The photograph was taken at an angle. The contributor is a female aged 50–59. The affected area is the leg, front of the torso, arm and back of the torso — 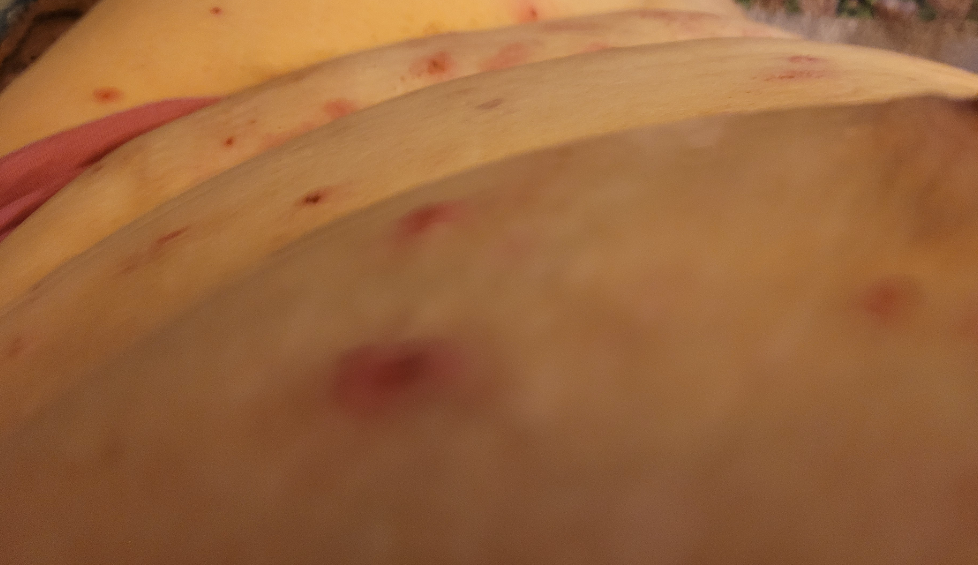diagnostic considerations = Prurigo nodularis (leading); Lichen Simplex Chronicus (considered); Pemphigus foliaceus (considered); Eczema (considered).